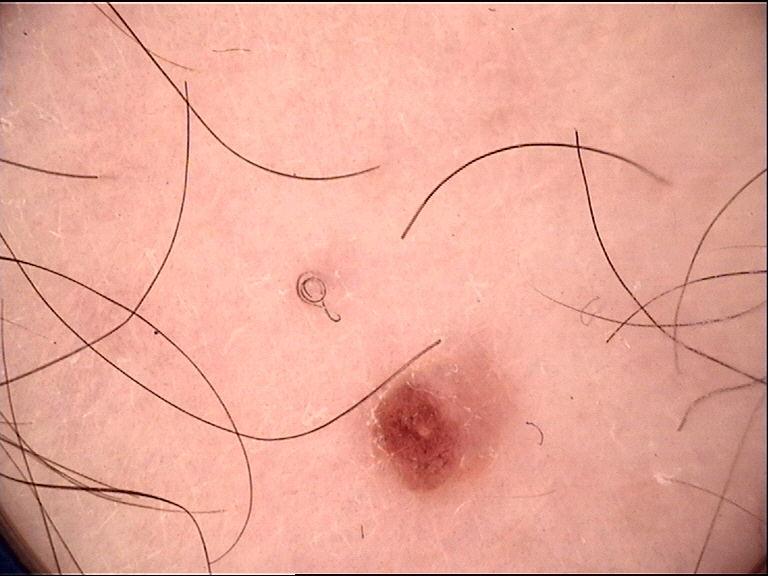A dermoscopic photograph of a skin lesion.
The morphology is that of a banal lesion.
Classified as a junctional nevus.